An image taken at a distance — 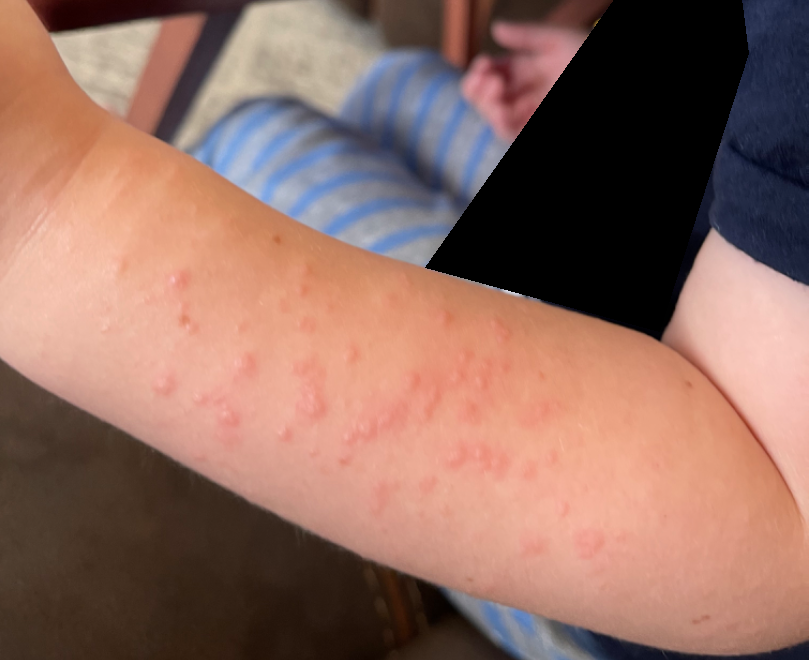diagnostic considerations=the primary impression is Urticaria; possibly Viral Exanthem.